The photo was captured at a distance. The affected area is the front of the torso and head or neck. Female contributor, age 30–39:
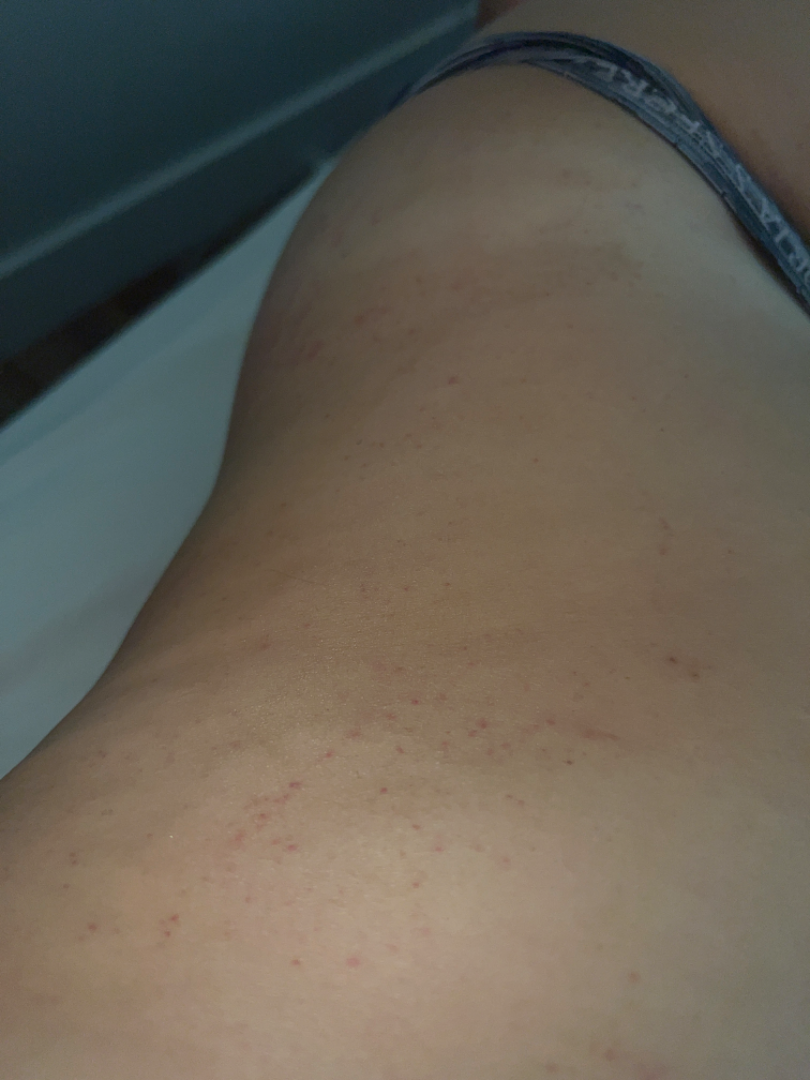The primary impression is Allergic Contact Dermatitis; also consider Eczema; the differential also includes Leukocytoclastic Vasculitis.